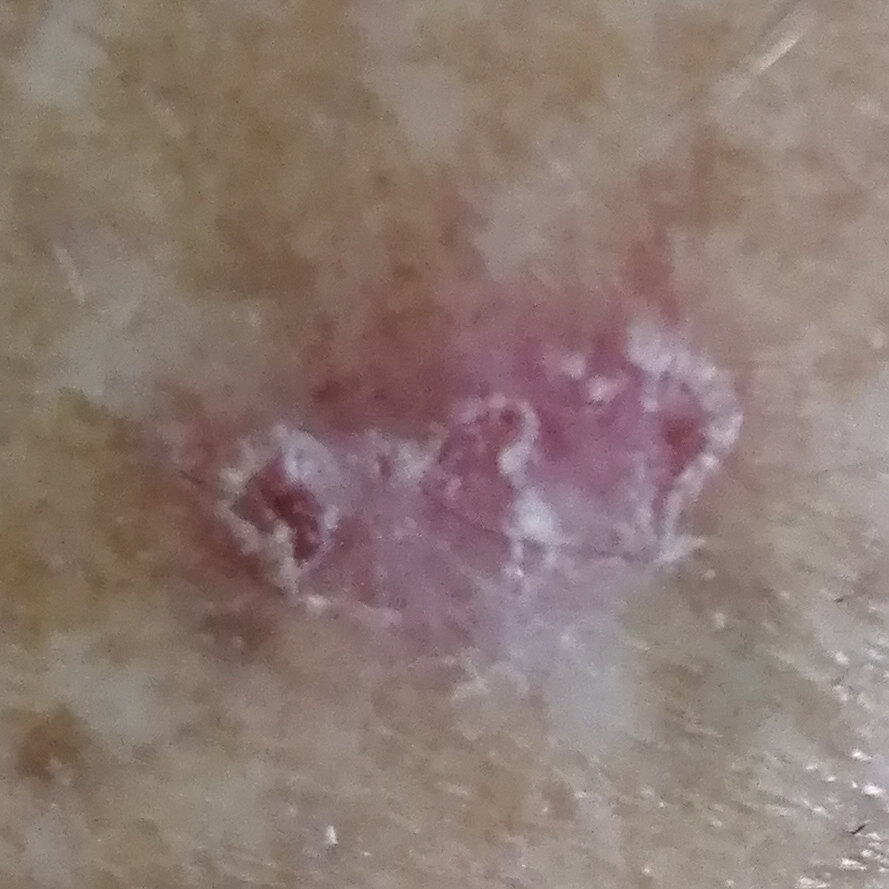Histopathology confirmed a basal cell carcinoma.